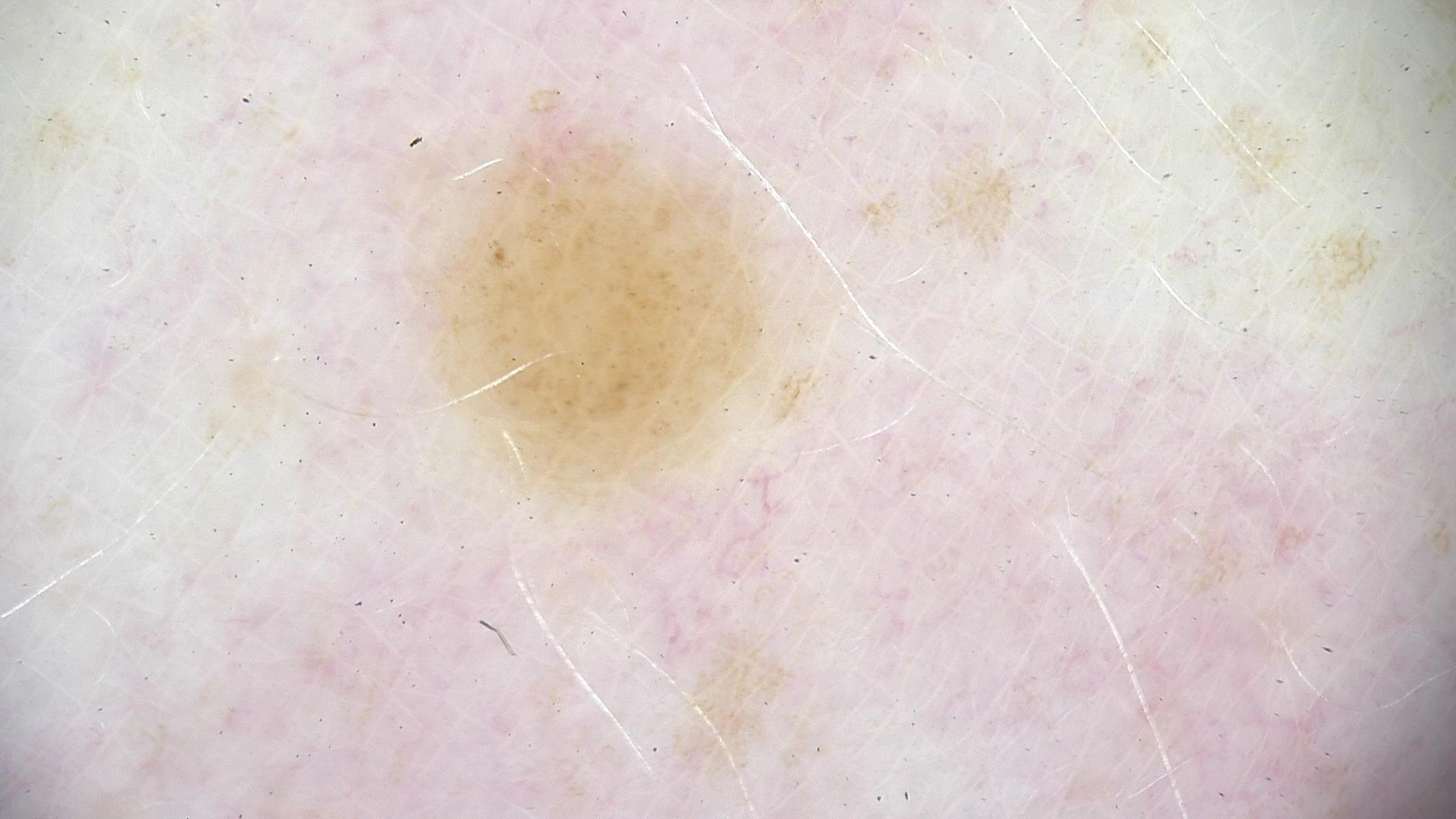- imaging — dermatoscopy
- lesion type — banal
- class — compound nevus (expert consensus)